The affected area is the leg · the contributor reports the lesion is rough or flaky and raised or bumpy · reported duration is less than one week · the lesion is associated with bothersome appearance · no relevant systemic symptoms · self-categorized by the patient as a rash · the contributor is 18–29, female · the photograph is a close-up of the affected area:
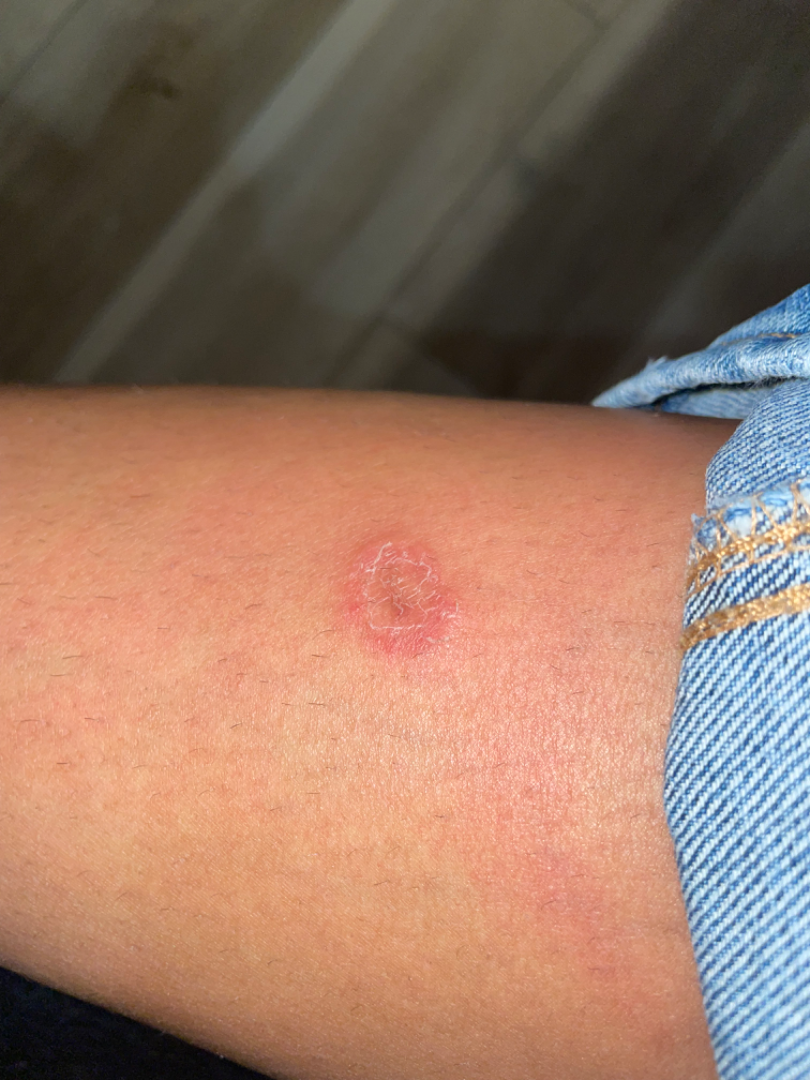Assessment: The dermatologist could not determine a likely condition from the photograph alone.